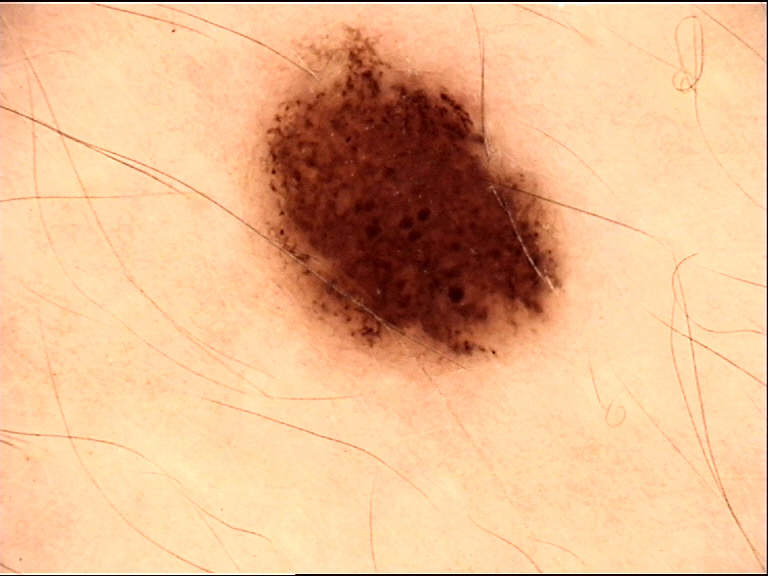Dermoscopy of a skin lesion. Diagnosed as a dysplastic compound nevus.